A skin lesion imaged with a dermatoscope.
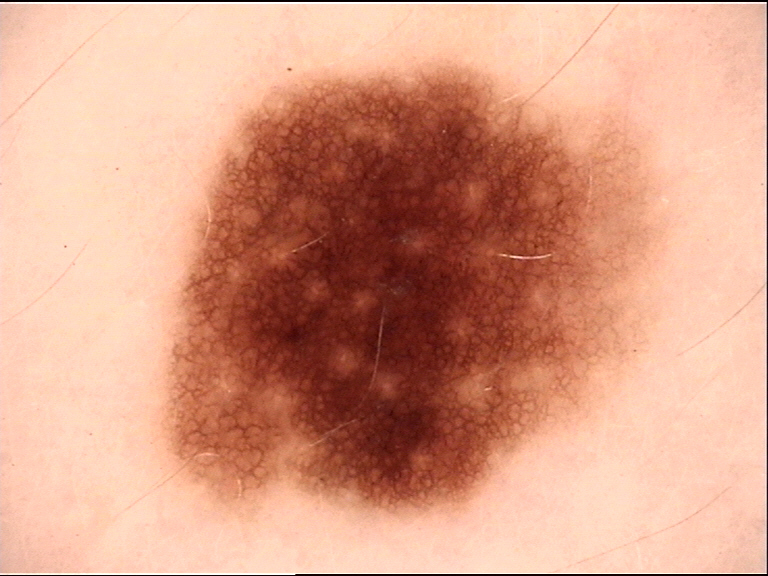{"diagnosis": {"name": "dysplastic junctional nevus", "code": "jd", "malignancy": "benign", "super_class": "melanocytic", "confirmation": "expert consensus"}}